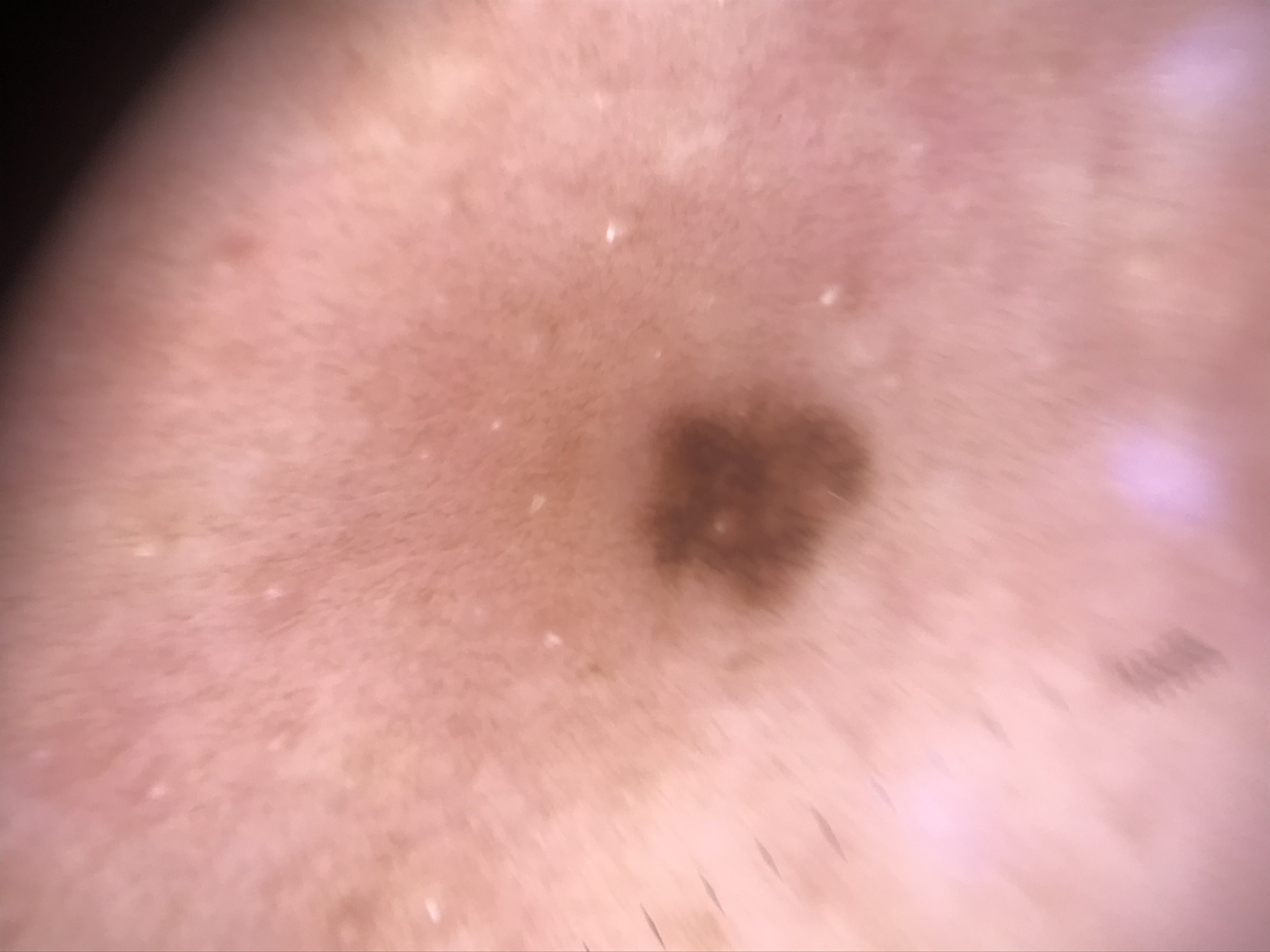Impression:
Labeled as a junctional nevus.